A dermoscopic photograph of a skin lesion:
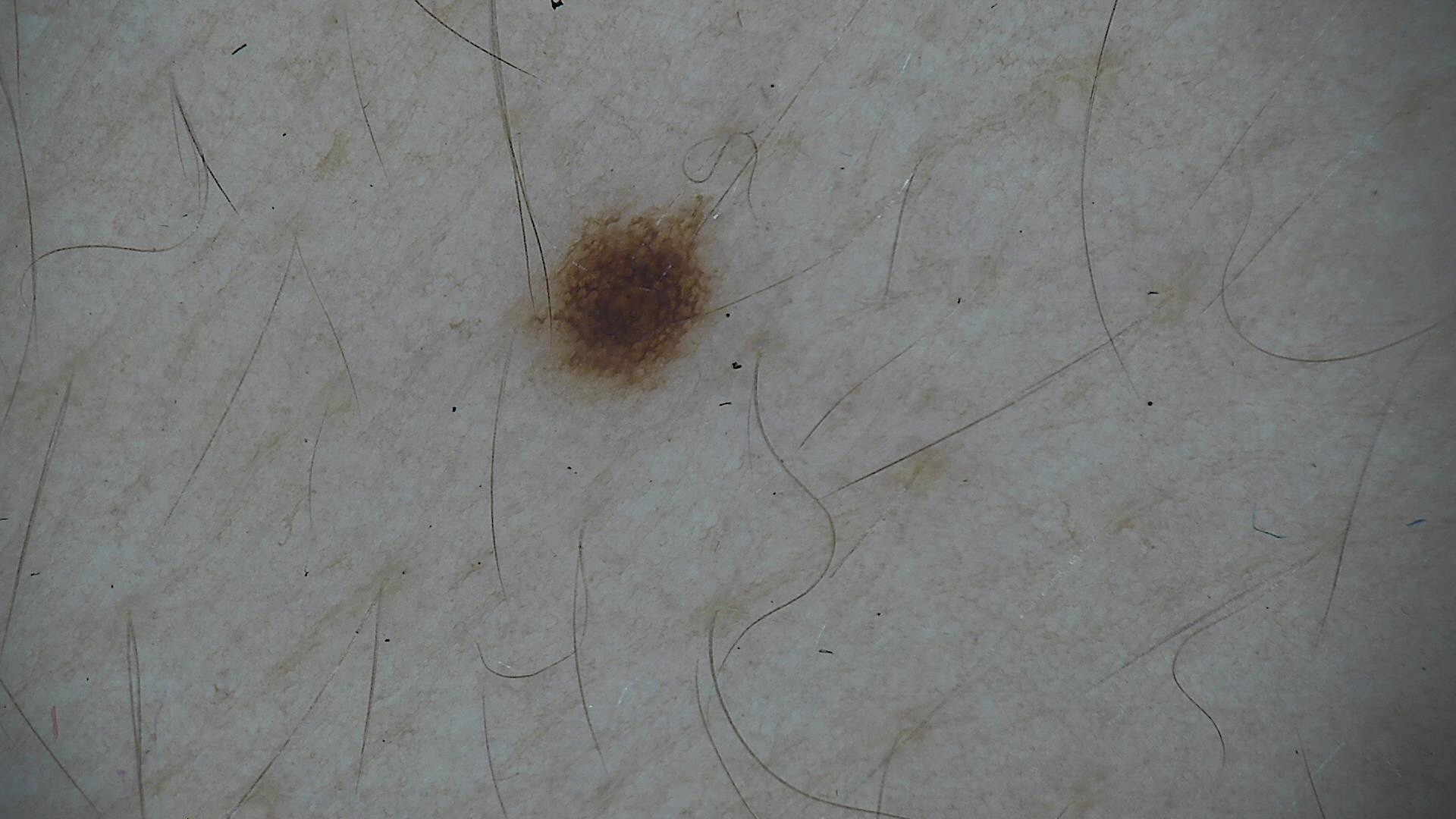diagnostic label: dysplastic junctional nevus (expert consensus).